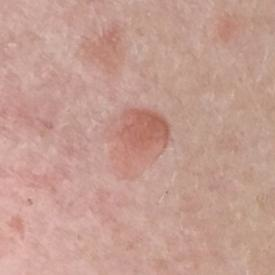image = clinical photograph
subject = female, in their mid-50s
location = the back
symptoms = elevation / no growth, no itching
diagnosis = nevus (clinical consensus)